The lesion involves the back of the torso and front of the torso; the photograph was taken at an angle; female patient, age 18–29:
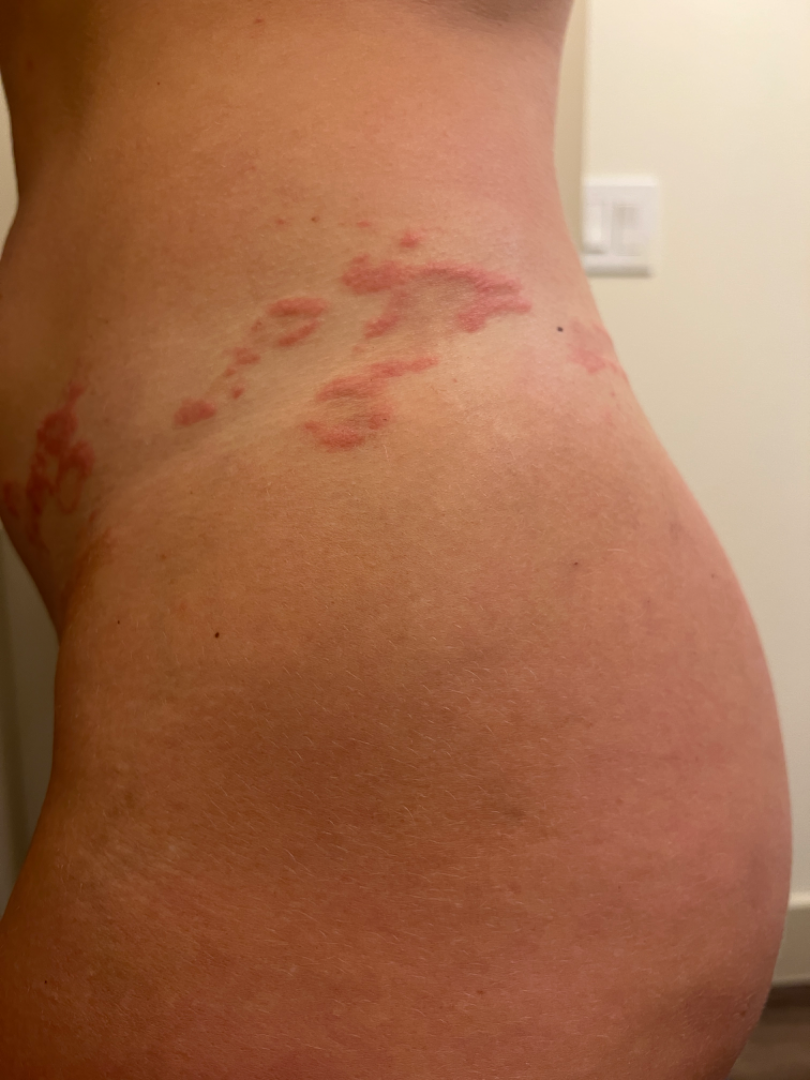Reviewed remotely by one dermatologist: the differential includes Granuloma annulare, Pemphigoid gestationis and Pruritic urticarial papules and plaques of pregnancy, with no clear leading consideration.